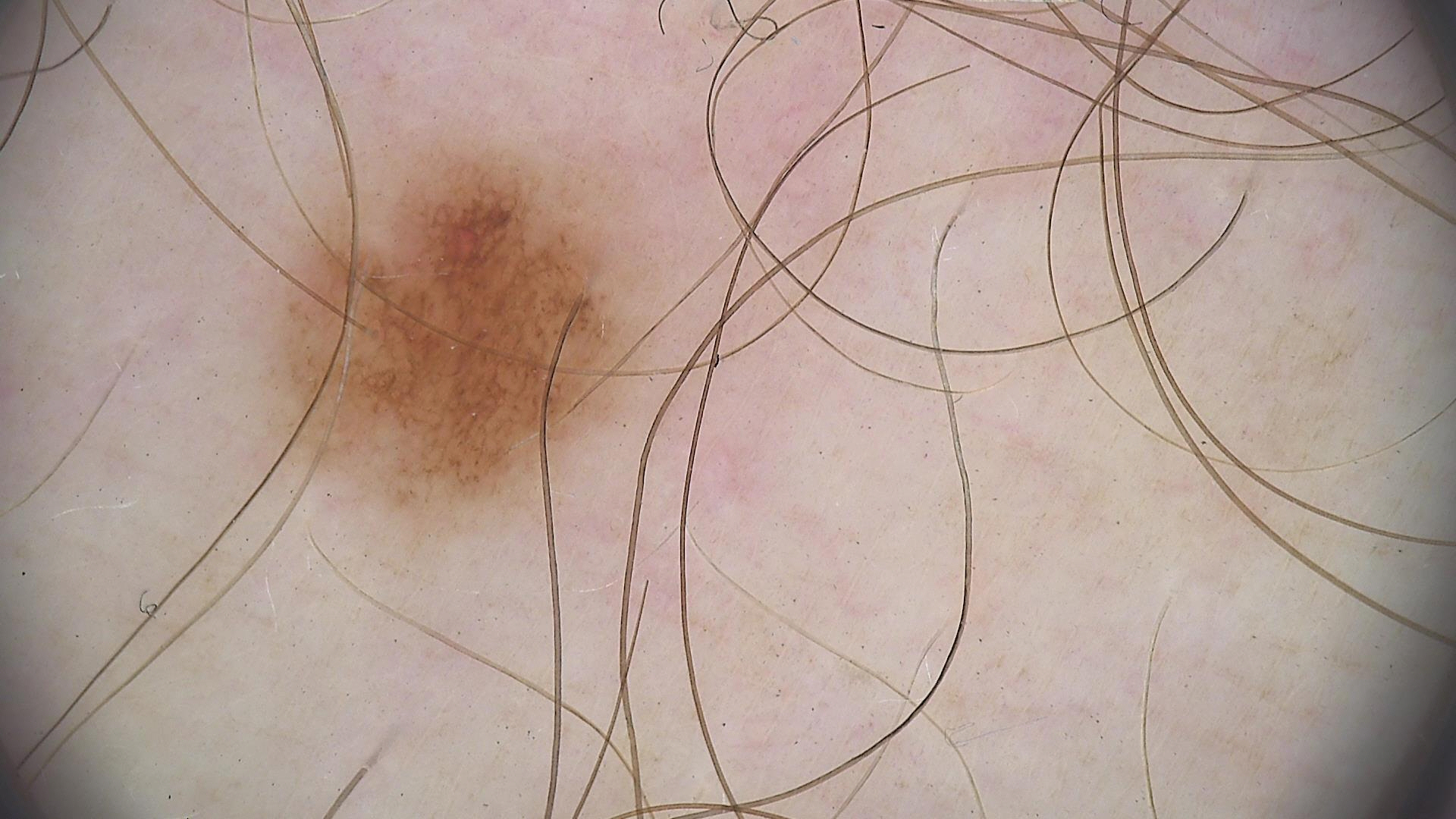{"image": "dermoscopy", "diagnosis": {"name": "dysplastic junctional nevus", "code": "jd", "malignancy": "benign", "super_class": "melanocytic", "confirmation": "expert consensus"}}